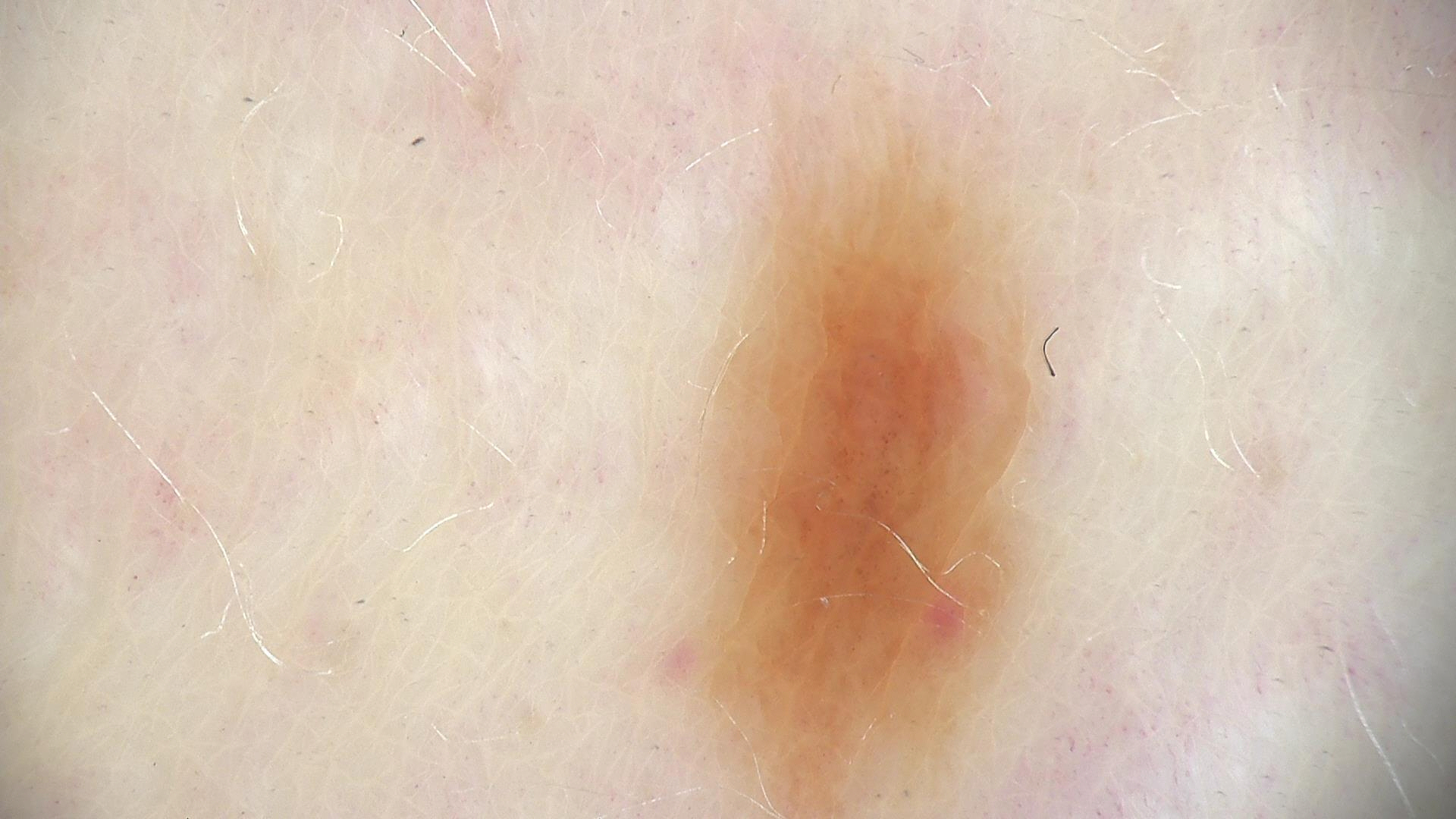image: dermatoscopy
diagnosis:
  name: dysplastic junctional nevus
  code: jd
  malignancy: benign
  super_class: melanocytic
  confirmation: expert consensus